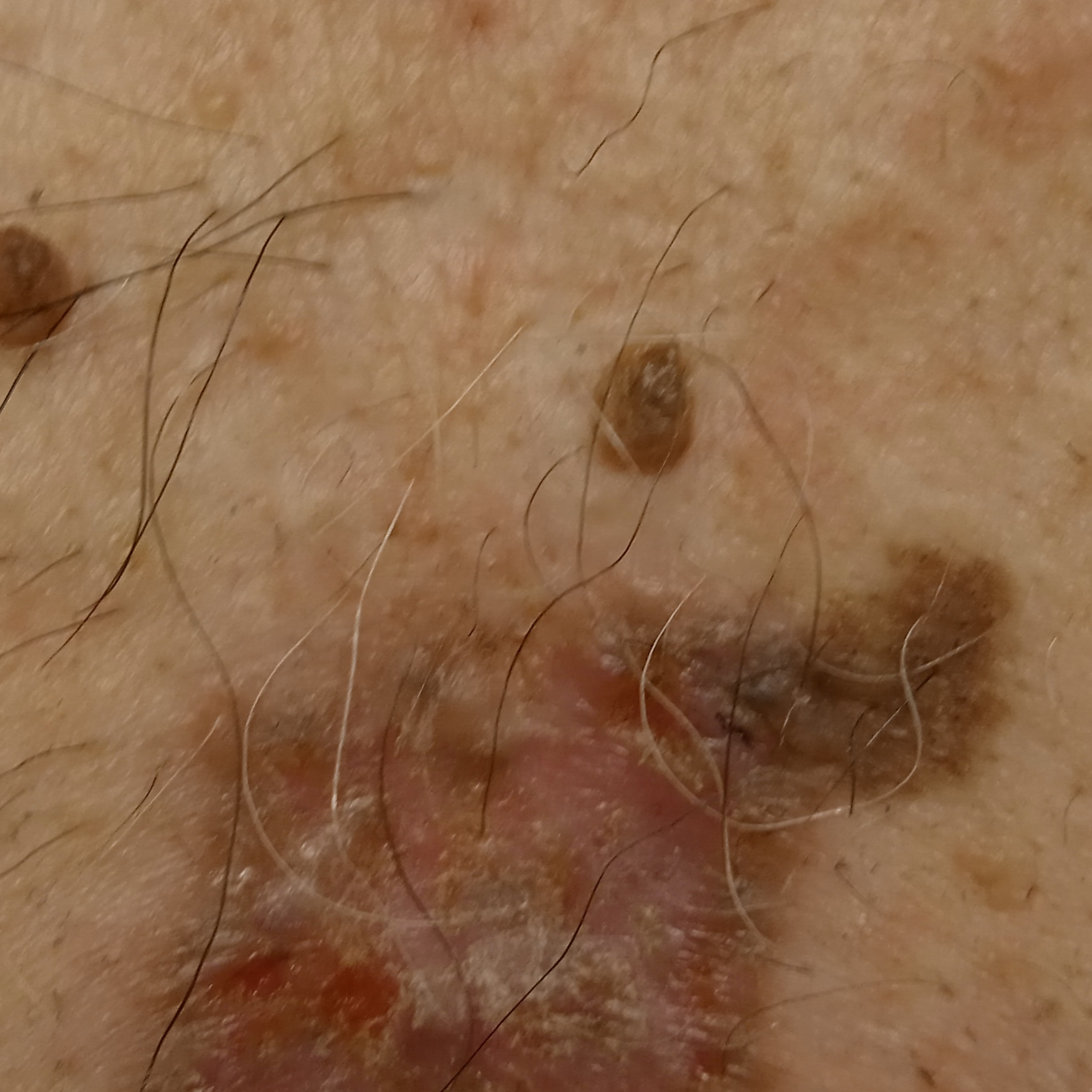Summary: On a questionnaire the patient reported a personal history of cancer. A moderate number of moles by the patient's own estimate. Referred with a clinical suspicion of basal cell carcinoma. A male subject 65 years old. A macroscopic clinical photograph of a skin lesion. The lesion is about 66 mm across. Conclusion: The biopsy diagnosis was a basal cell carcinoma, following a punch biopsy, with tumor thickness 0.3 mm.